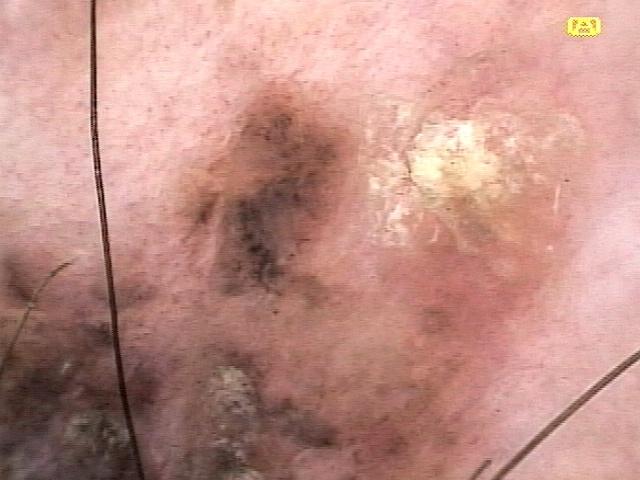imaging = dermatoscopic image
subject = male, aged around 85 or older
FST = II
risk factors = a previous melanoma
location = a lower extremity
diagnostic label = Melanoma (biopsy-proven)